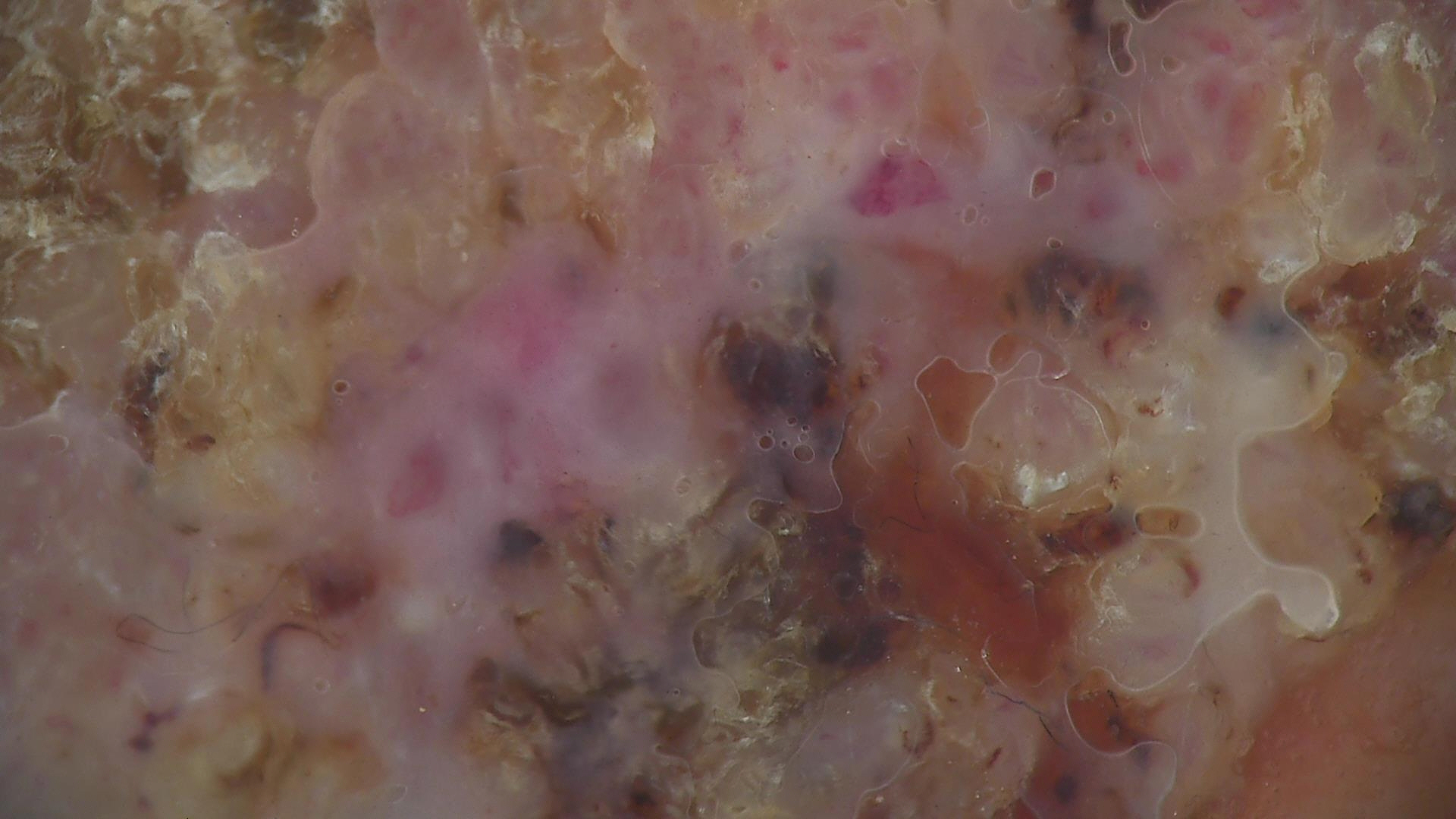Conclusion: Histopathology confirmed a squamous cell carcinoma.